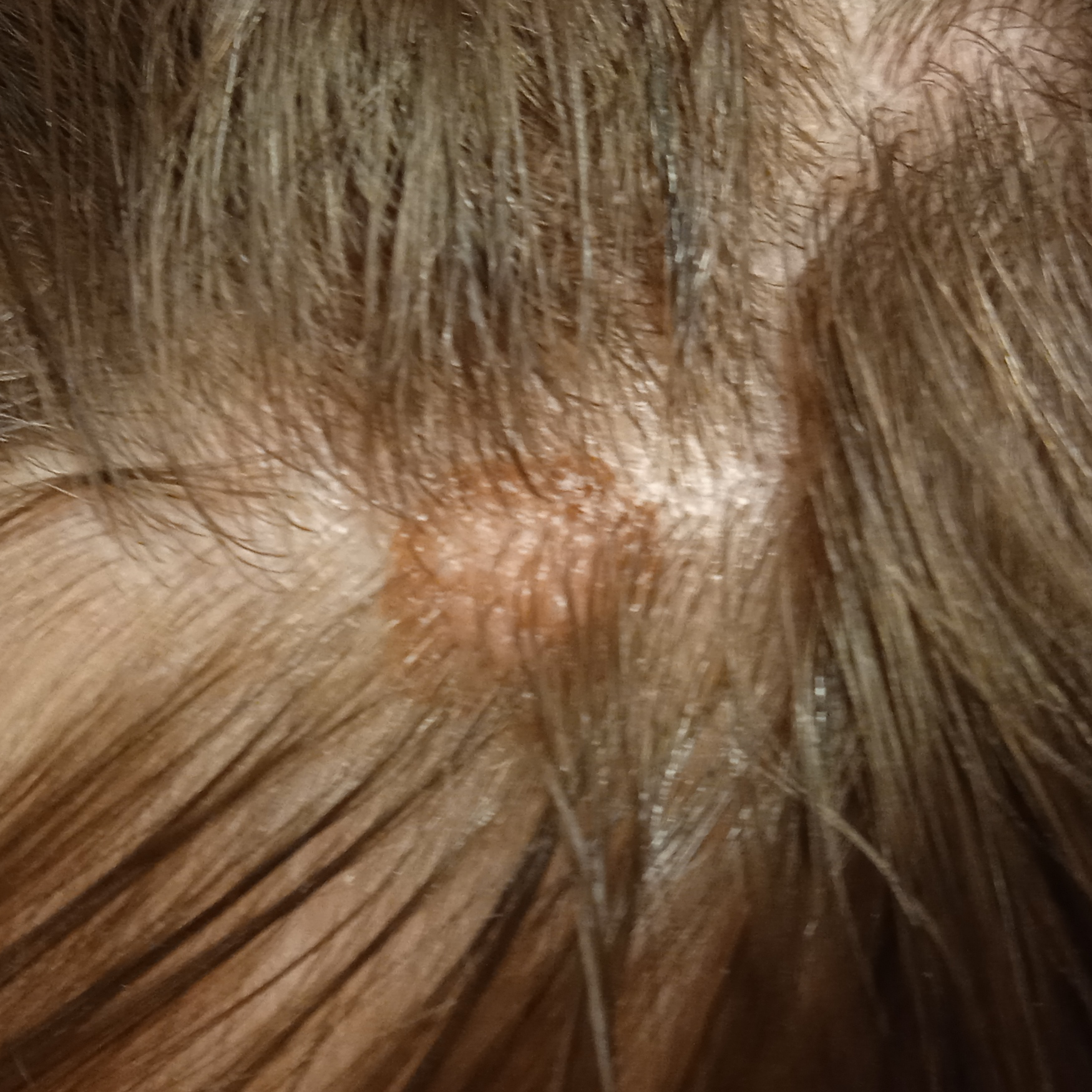The diagnostic impression was a melanocytic nevus.